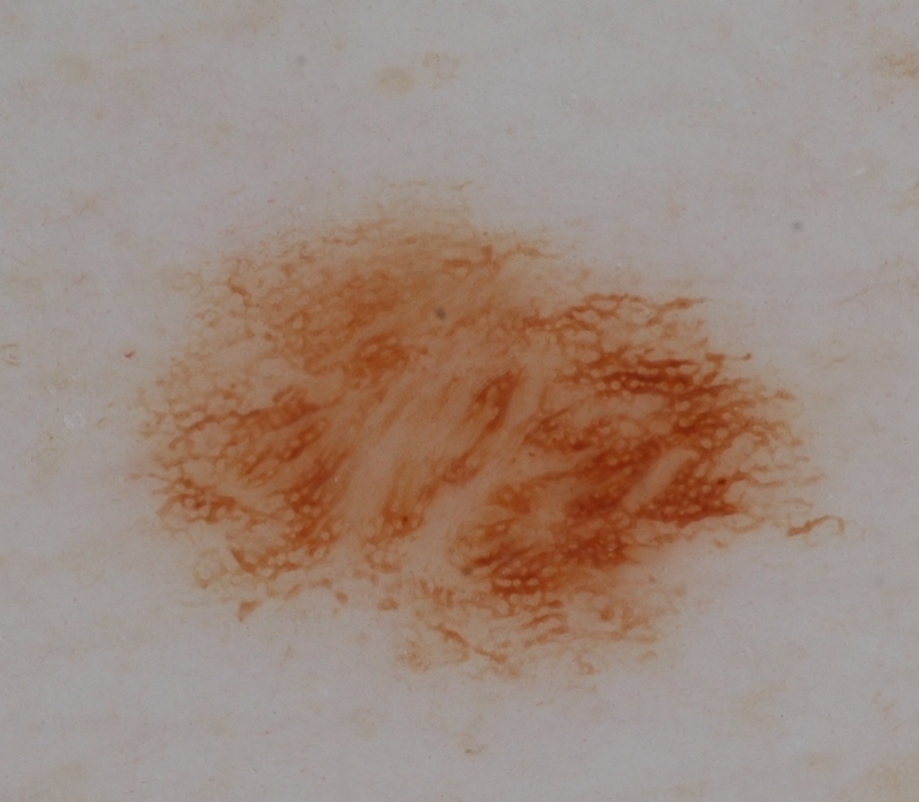| feature | finding |
|---|---|
| imaging | dermatoscopic image of a skin lesion |
| extent | ~32% of the field |
| lesion bbox | 122, 194, 825, 681 |
| dermoscopic findings | globules and pigment network; absent: negative network, milia-like cysts, and streaks |
| assessment | a melanocytic nevus, a benign lesion |